The patient is FST II · contact-polarized dermoscopy of a skin lesion · a female subject aged 63-67: 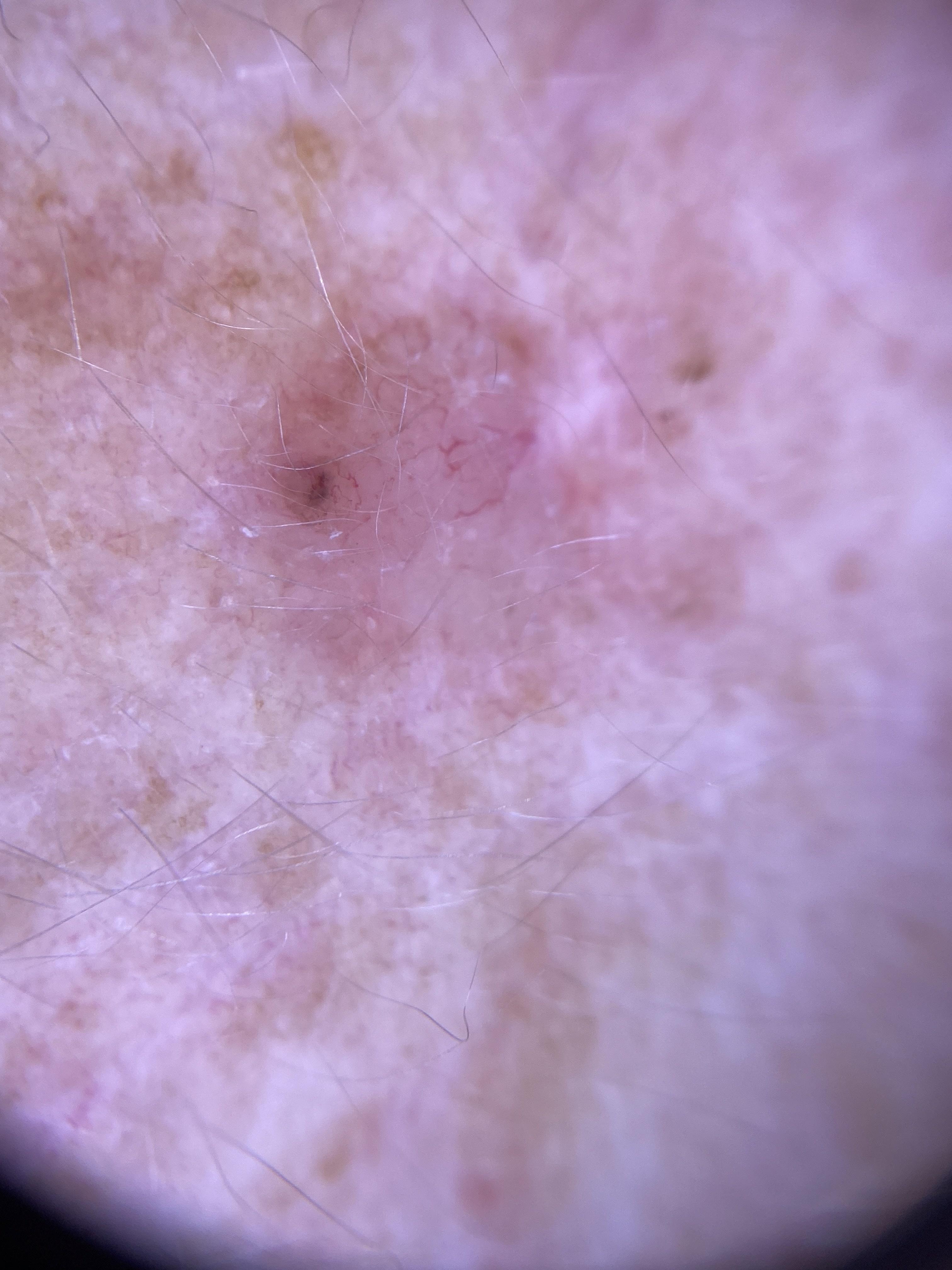anatomic site = the head or neck, diagnostic label = Basal cell carcinoma (biopsy-proven).